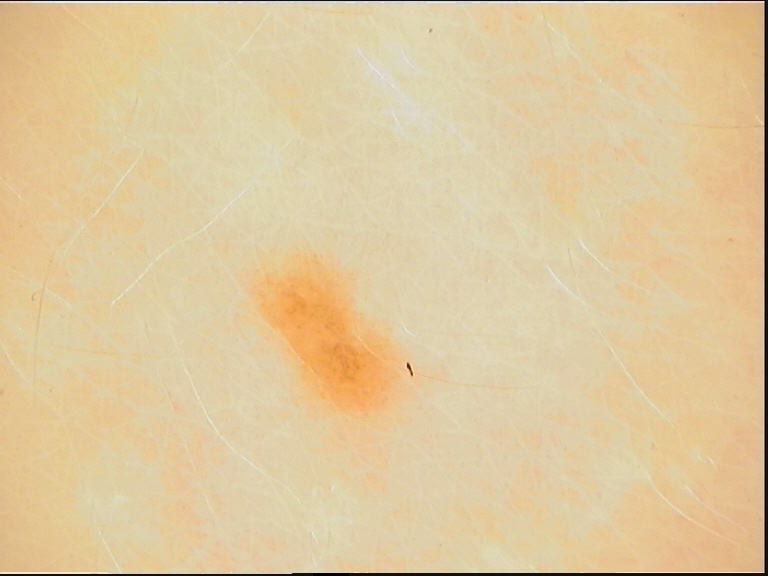Findings: A dermoscopic close-up of a skin lesion. This is a banal lesion. Impression: Diagnosed as a junctional nevus.